A clinical photograph of a skin lesion · a female subject age 55 · on a questionnaire the patient reported a prior organ transplant, immunosuppression, no personal history of skin cancer, and no family history of skin cancer · the patient describes having a moderate number of moles · the patient says their skin reddens painfully with sun exposure — 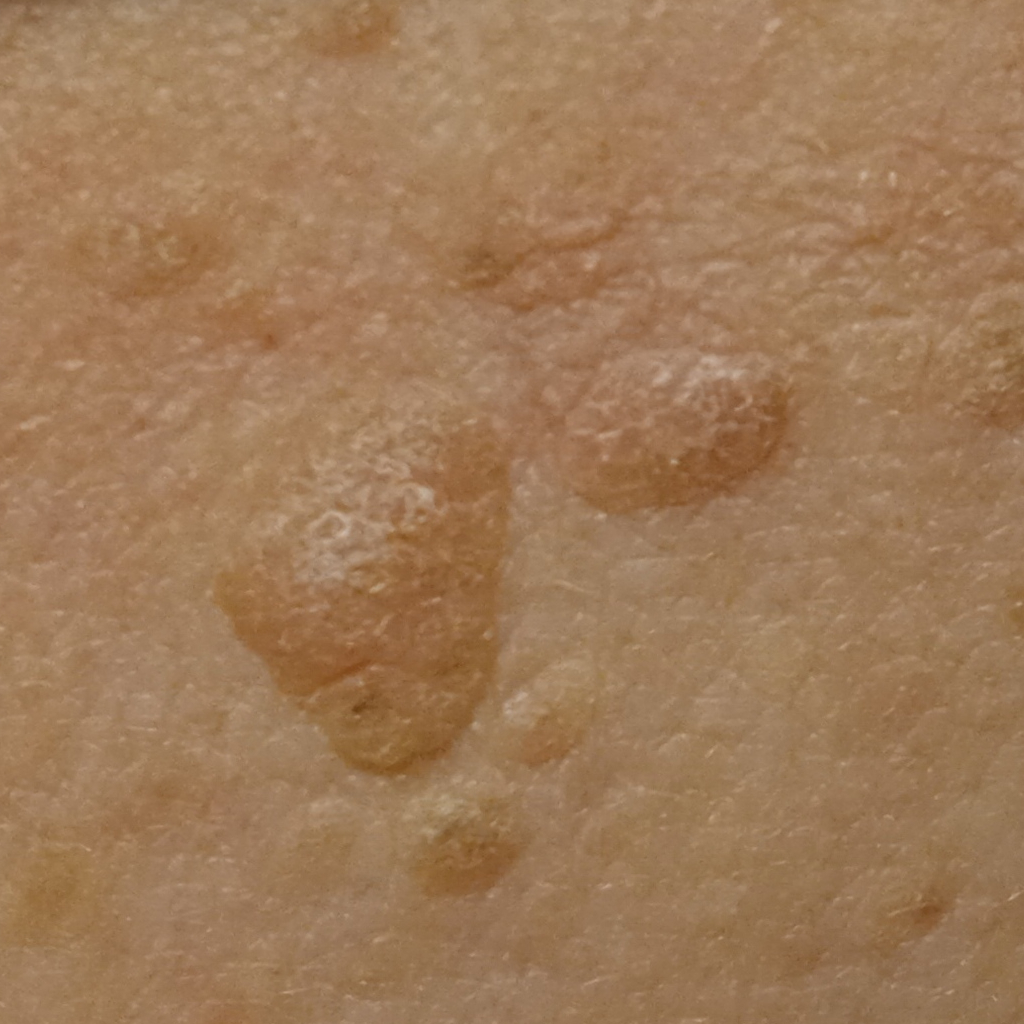The lesion is located on the back. The lesion measures approximately 10.6 mm. The lesion was assessed as a seborrheic keratosis.